Self-categorized by the patient as a rash, located on the front of the torso, the lesion is associated with burning and itching, reported duration is less than one week, the photograph is a close-up of the affected area.
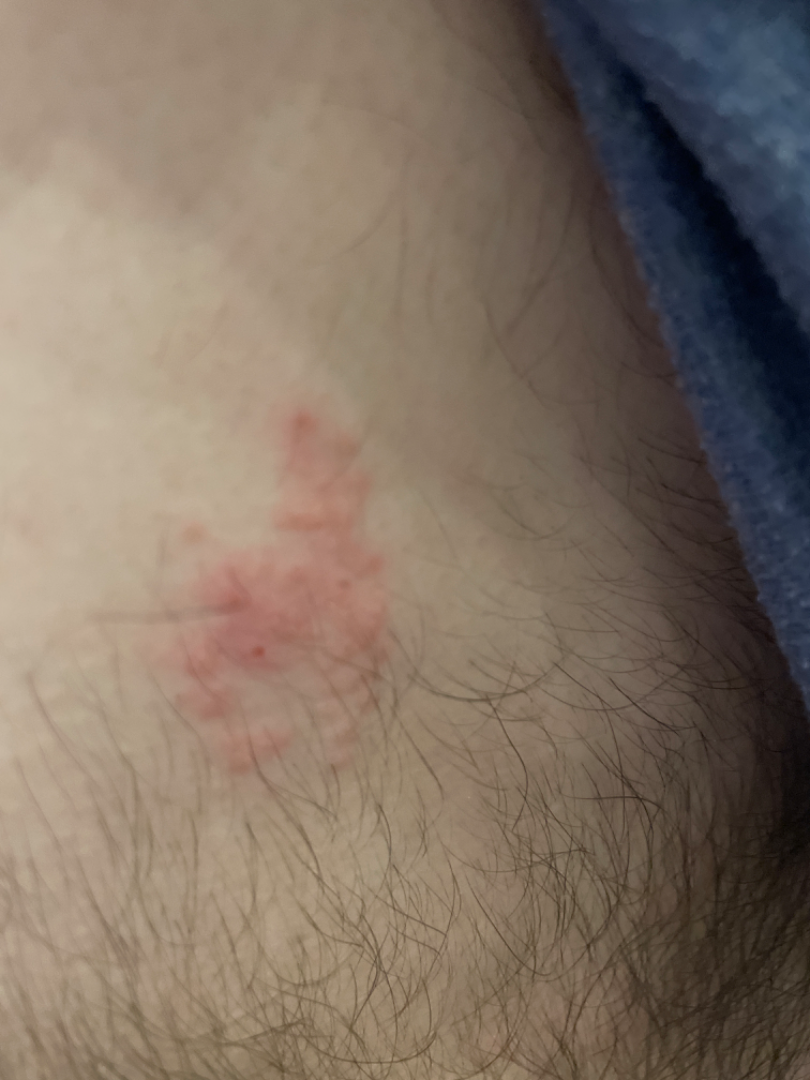Q: What was the assessment?
A: ungradable on photographic review